The front of the torso is involved · texture is reported as rough or flaky · female contributor, age 50–59 · the patient indicates pain · this image was taken at an angle · the patient indicates the condition has been present for less than one week:
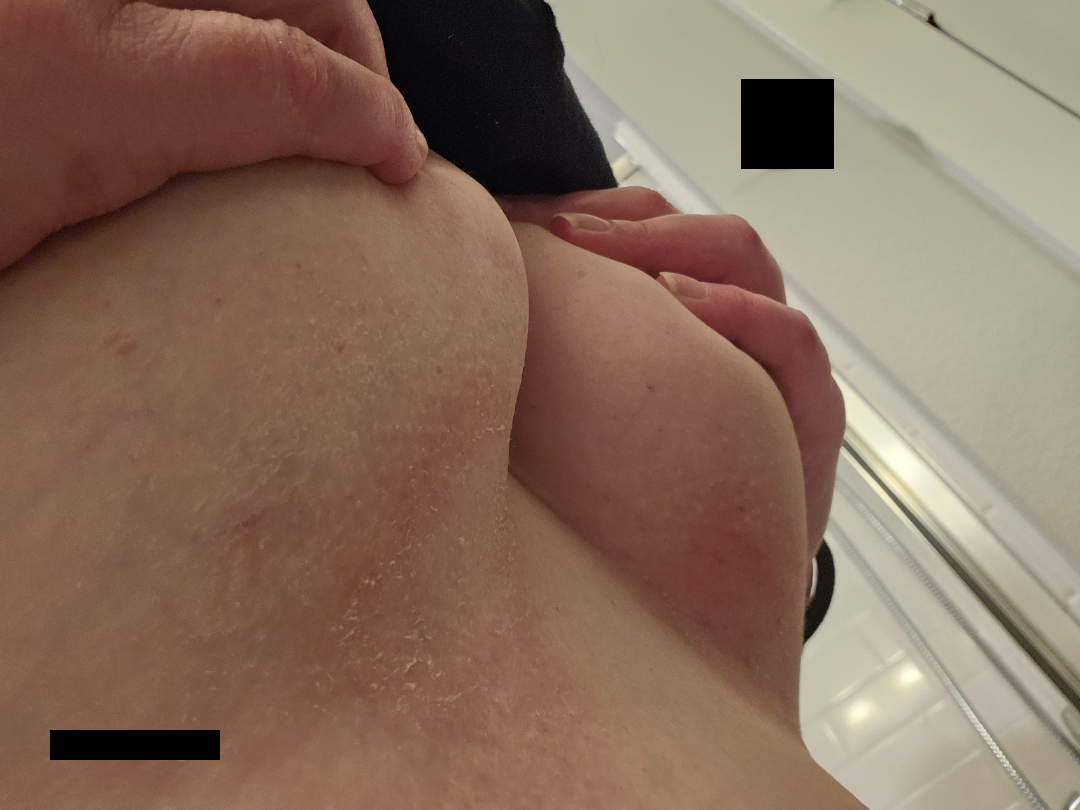On independent review by the dermatologists, most consistent with Intertrigo; with consideration of Psoriasis; lower on the differential is Candida; less probable is Seborrheic Dermatitis.